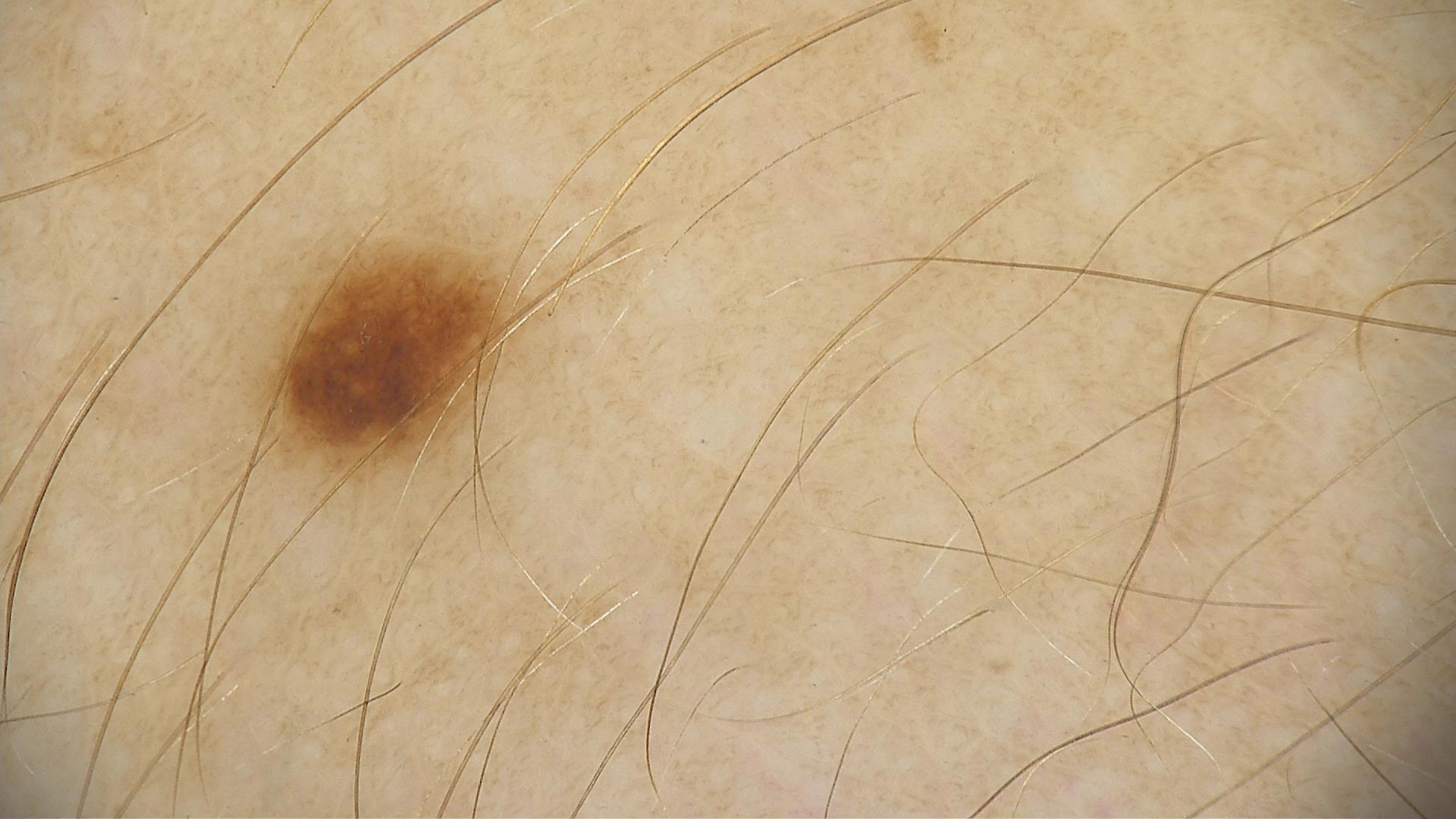Diagnosed as a dysplastic junctional nevus.